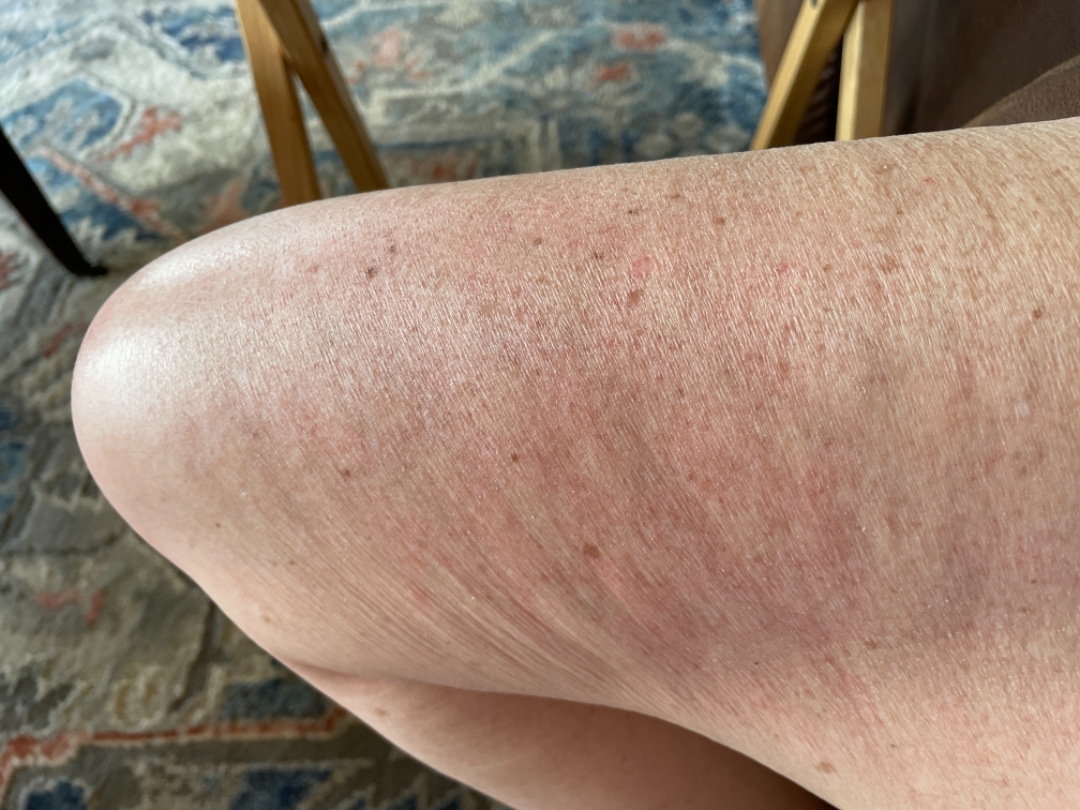assessment=unable to determine
present for=about one day
contributor=female, age 60–69
lesion symptoms=none reported
texture=flat
image framing=at a distance
location=leg
patient describes the issue as=skin that appeared healthy to them